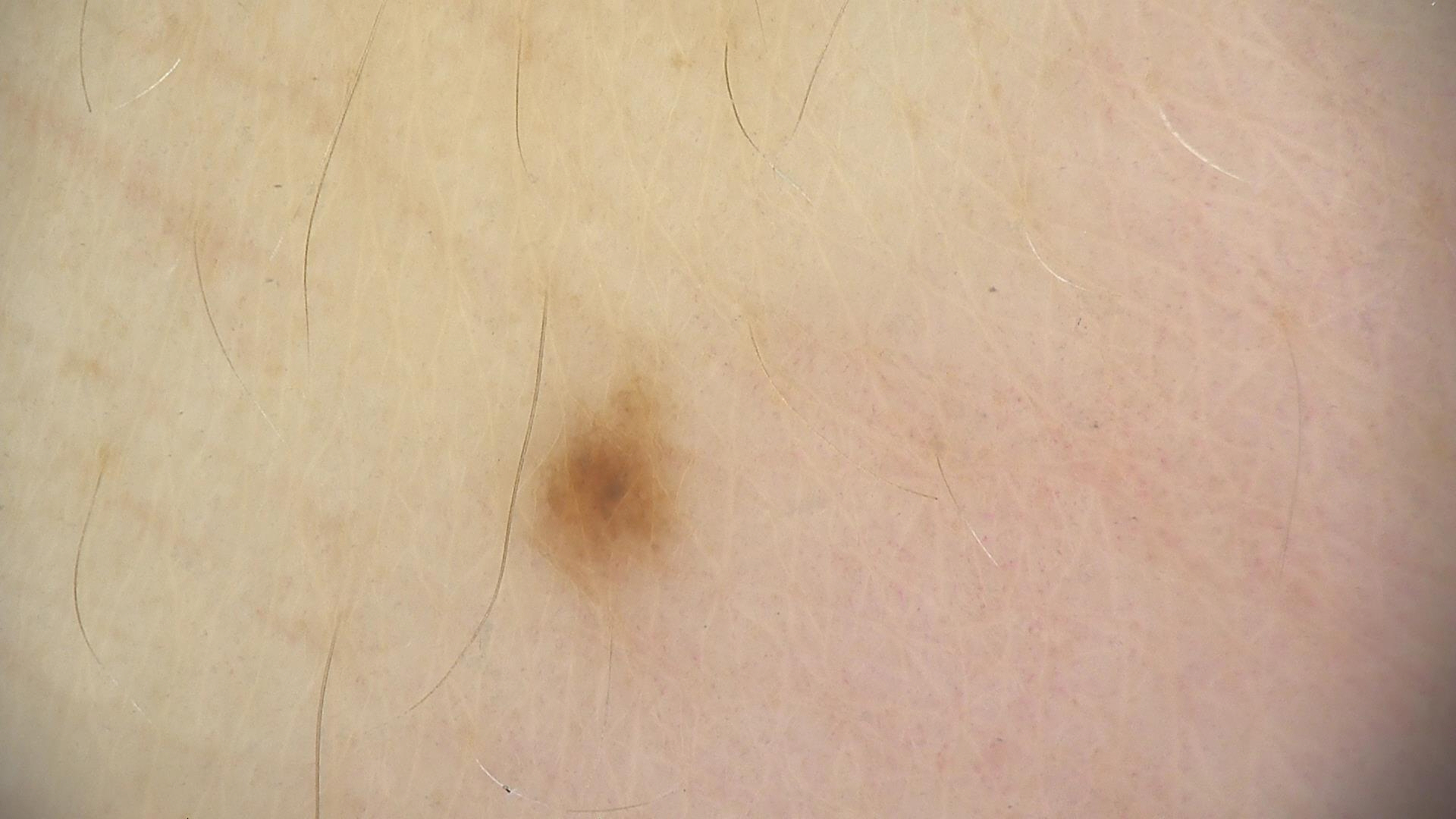A dermoscopic photograph of a skin lesion. The diagnostic label was a dysplastic junctional nevus.